Collected as part of a research study, without a referral diagnosis; the patient says their skin reddens painfully with sun exposure; a clinical photograph of a skin lesion; a female subject 72 years of age; by self-report, immunosuppression, a personal history of cancer, and a personal history of skin cancer.
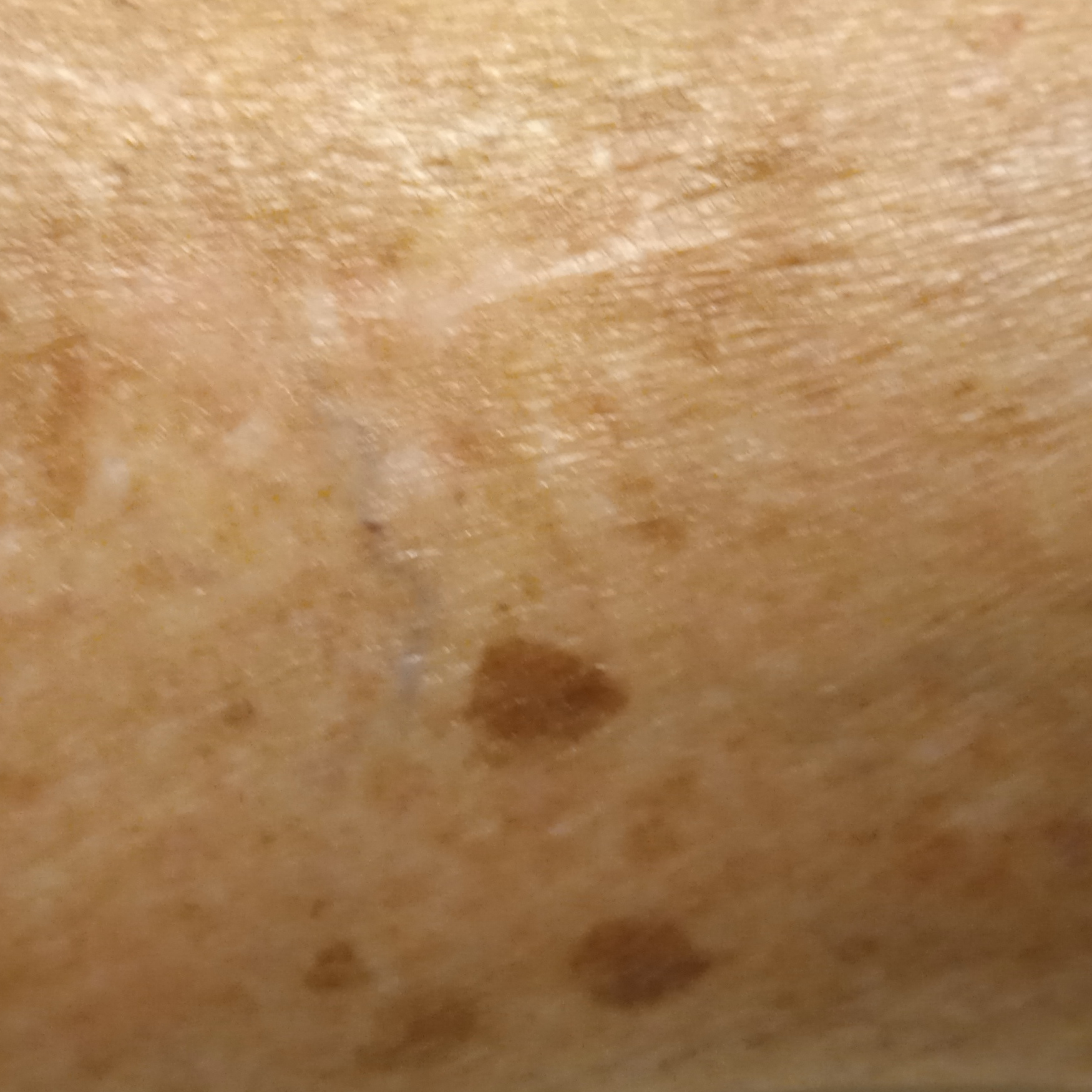The lesion is on a leg. The lesion measures approximately 6.6 mm. The consensus diagnosis for this lesion was a melanocytic nevus.